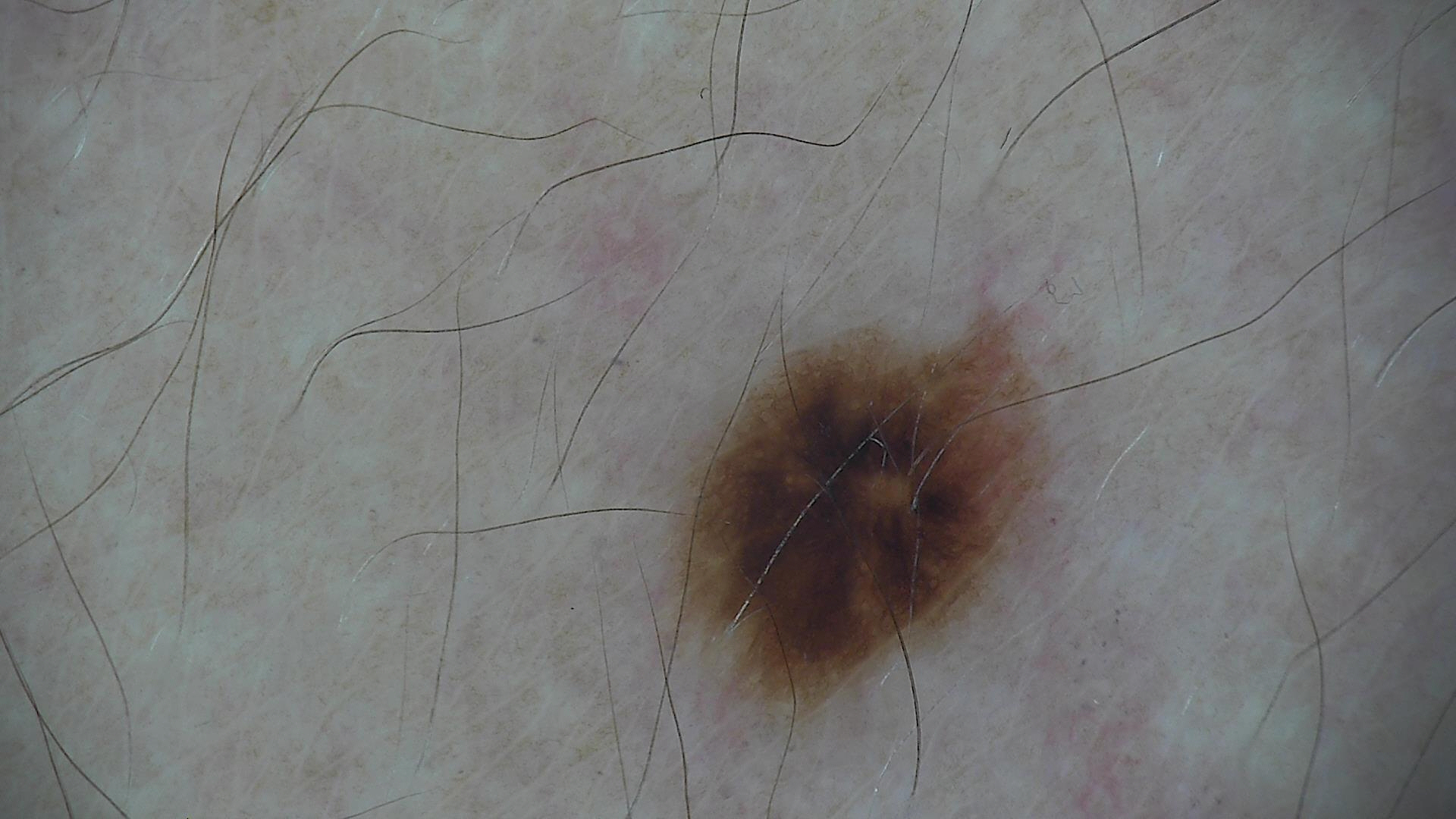Q: What is the imaging modality?
A: dermatoscopy
Q: What is the diagnosis?
A: dysplastic junctional nevus (expert consensus)